The patient is 18–29, female; the photo was captured at an angle; the lesion involves the leg: 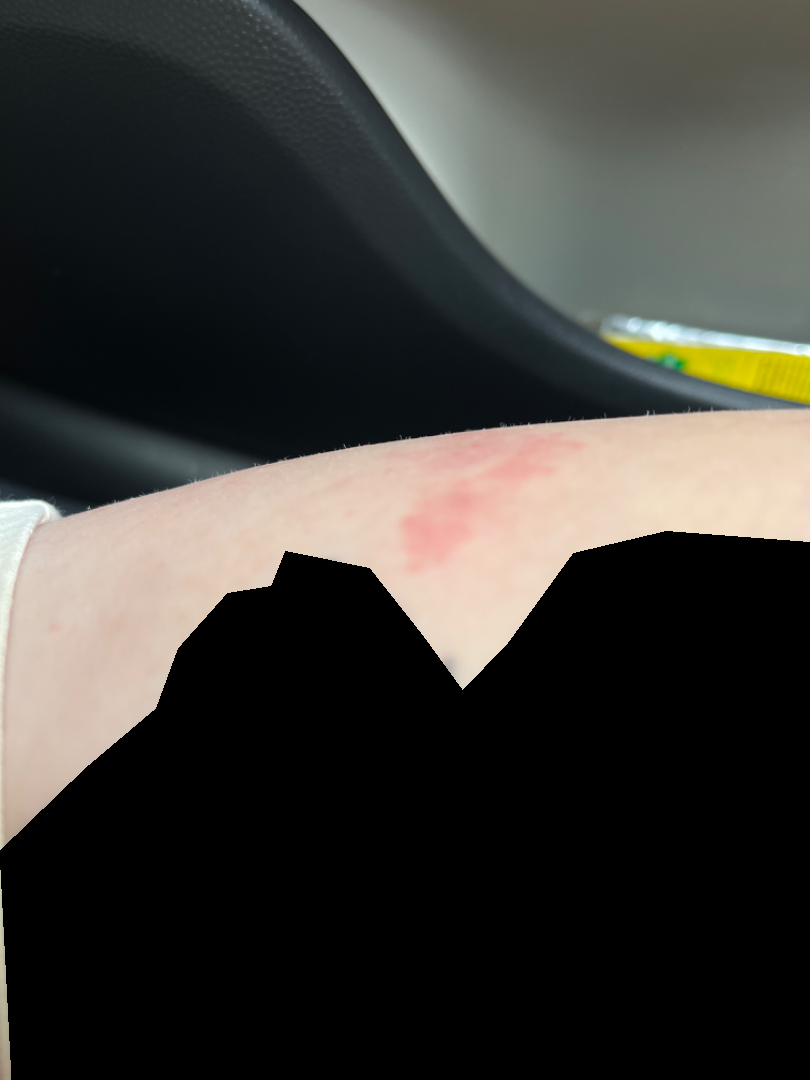assessment: the impression was split between Eczema and Allergic Contact Dermatitis.